A male subject about 65 years old; the chart documents a previous melanoma; a dermoscopic image of a skin lesion; the patient was assessed as Fitzpatrick skin type II — 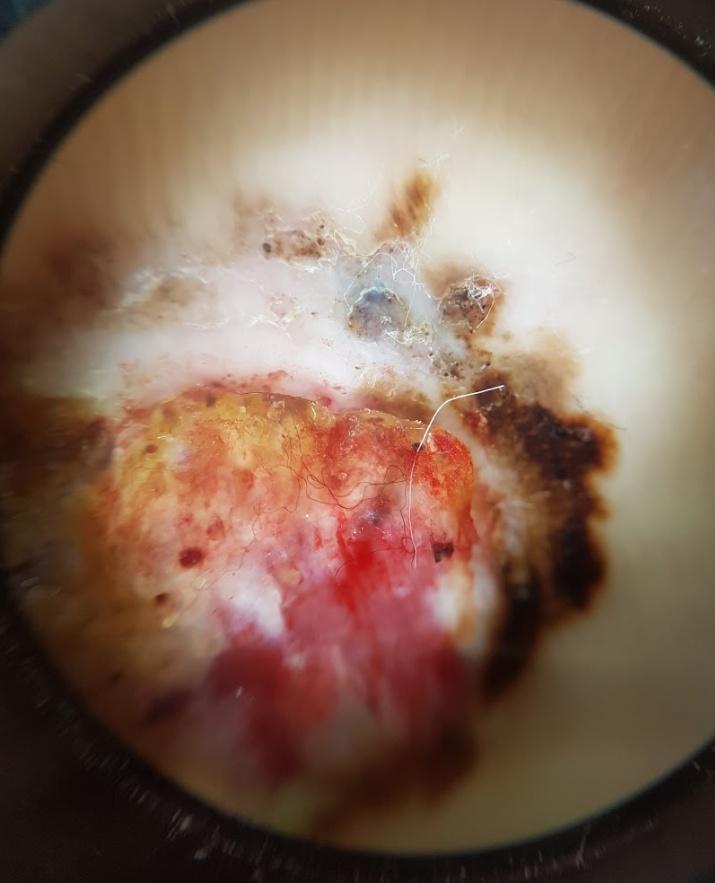{"diagnosis": {"name": "Melanoma", "malignancy": "malignant", "confirmation": "histopathology"}}